The patient is a male about 50 years old · a dermoscopic view of a skin lesion: 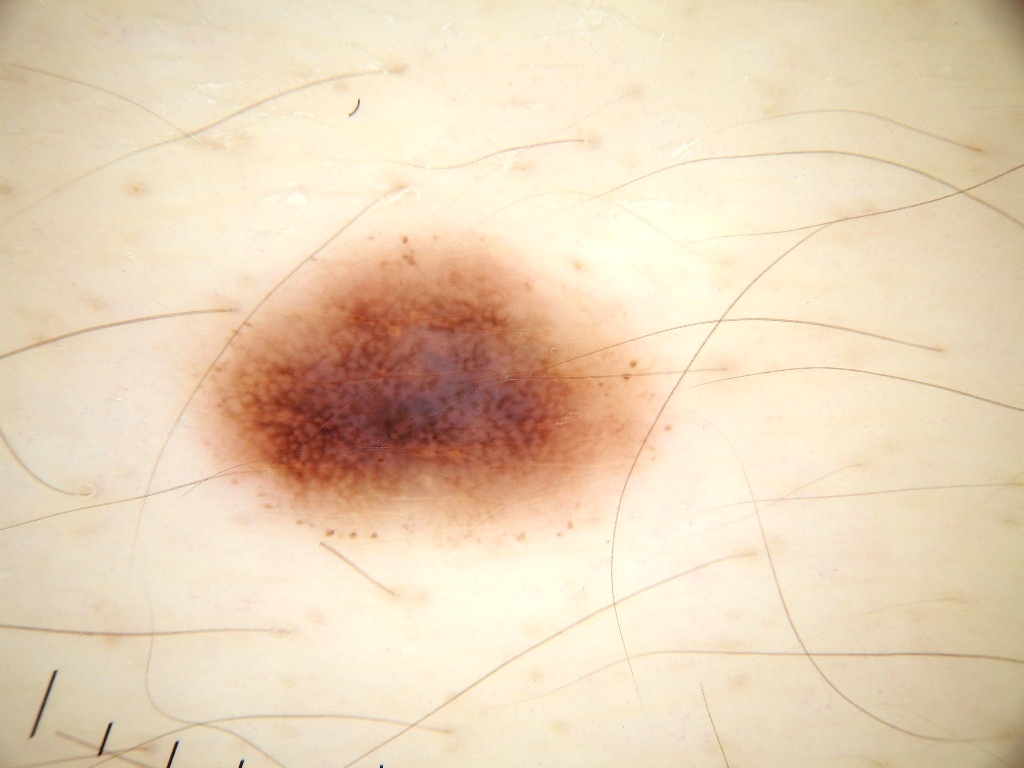dermoscopic pattern = negative network, globules, and pigment network; absent: milia-like cysts and streaks | size = ~19% of the field | bounding box = bbox=[156, 214, 694, 572] | impression = a melanocytic nevus, a benign skin lesion.